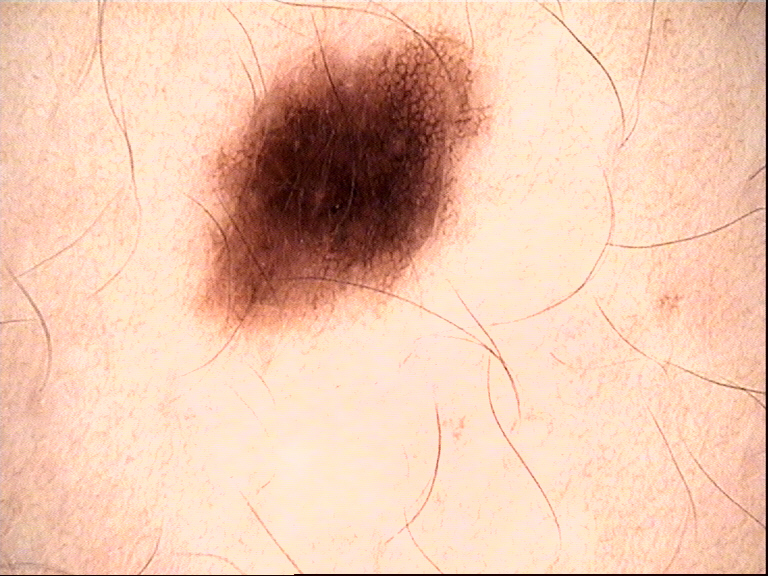modality = dermatoscopy, label = dysplastic junctional nevus (expert consensus).